Few moles overall by the patient's own estimate; the patient says their skin reddens with sun exposure; a dermoscopy image of a skin lesion; collected as part of a research study, without a referral diagnosis; by self-report, a personal history of cancer; a male subject aged 78.
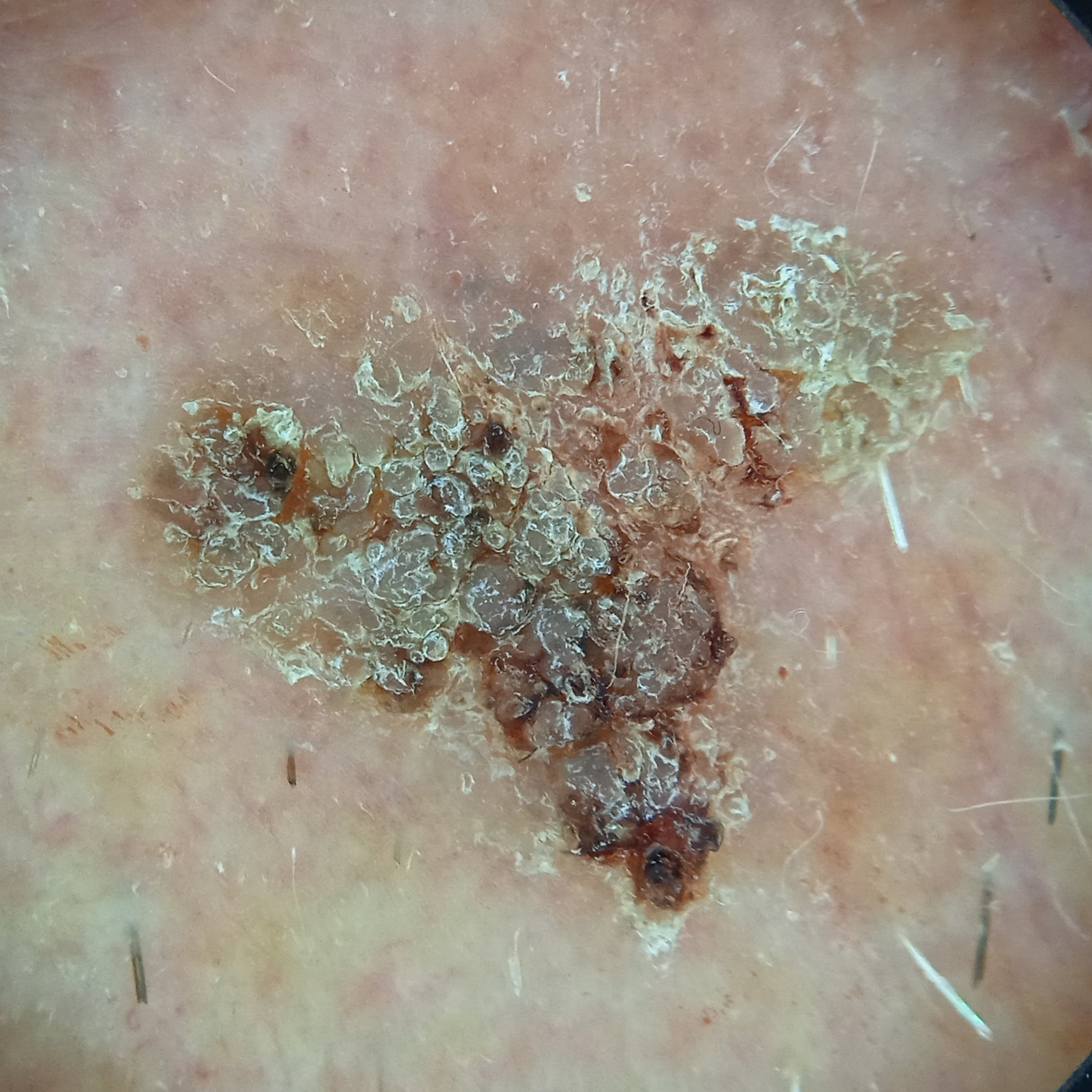* location: the face
* diameter: 10.5 mm
* diagnosis: seborrheic keratosis (dermatologist consensus)